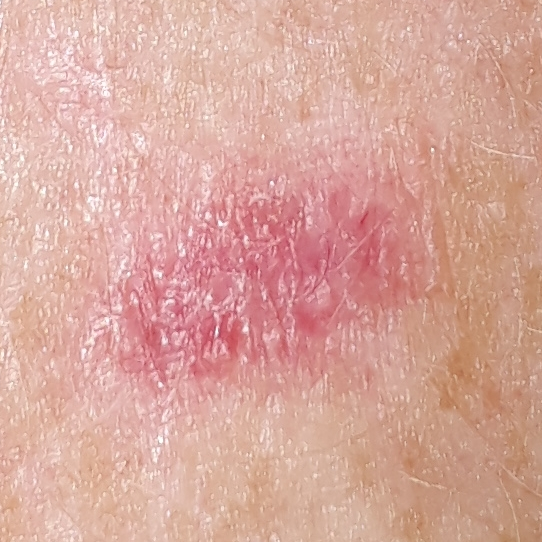{"patient": {"age": 56, "gender": "female"}, "image": "clinical photo", "lesion_location": "a forearm", "diagnosis": {"name": "basal cell carcinoma", "code": "BCC", "malignancy": "malignant", "confirmation": "histopathology"}}